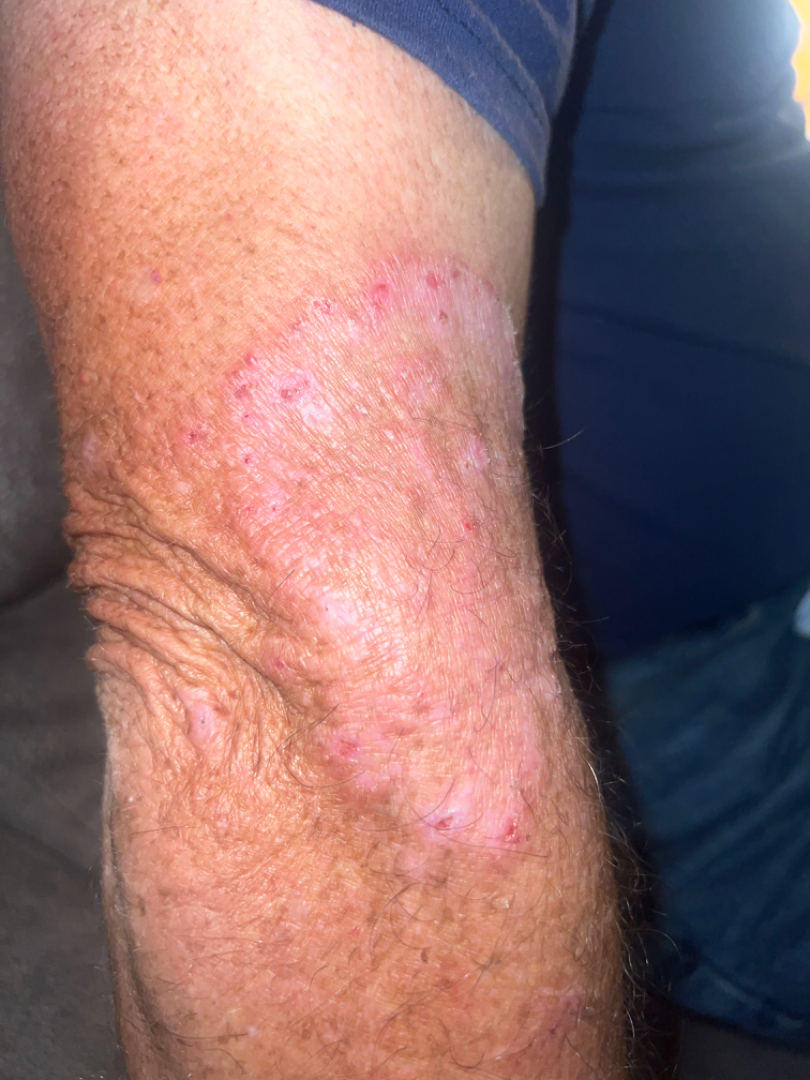• skin tone — FST III
• shot type — at an angle
• dermatologist impression — the leading consideration is Tinea; an alternative is Granuloma annulare; also on the differential is Psoriasis